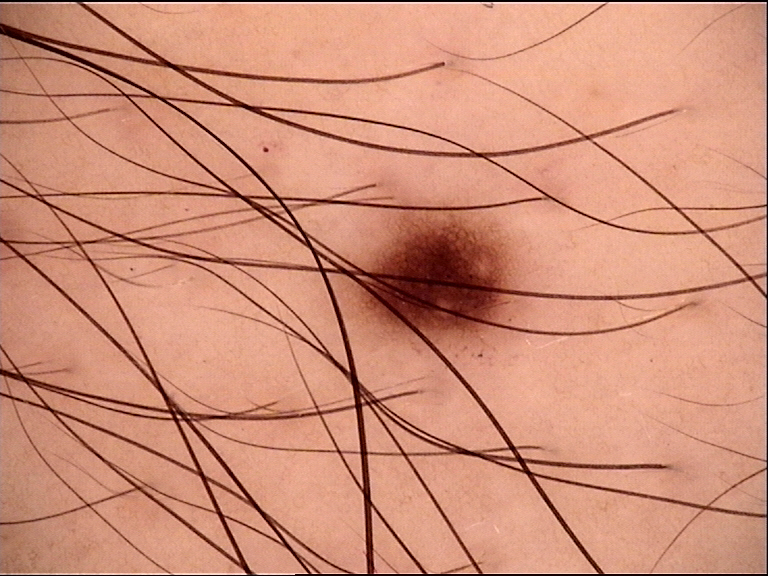diagnosis:
  name: junctional nevus
  code: jb
  malignancy: benign
  super_class: melanocytic
  confirmation: expert consensus